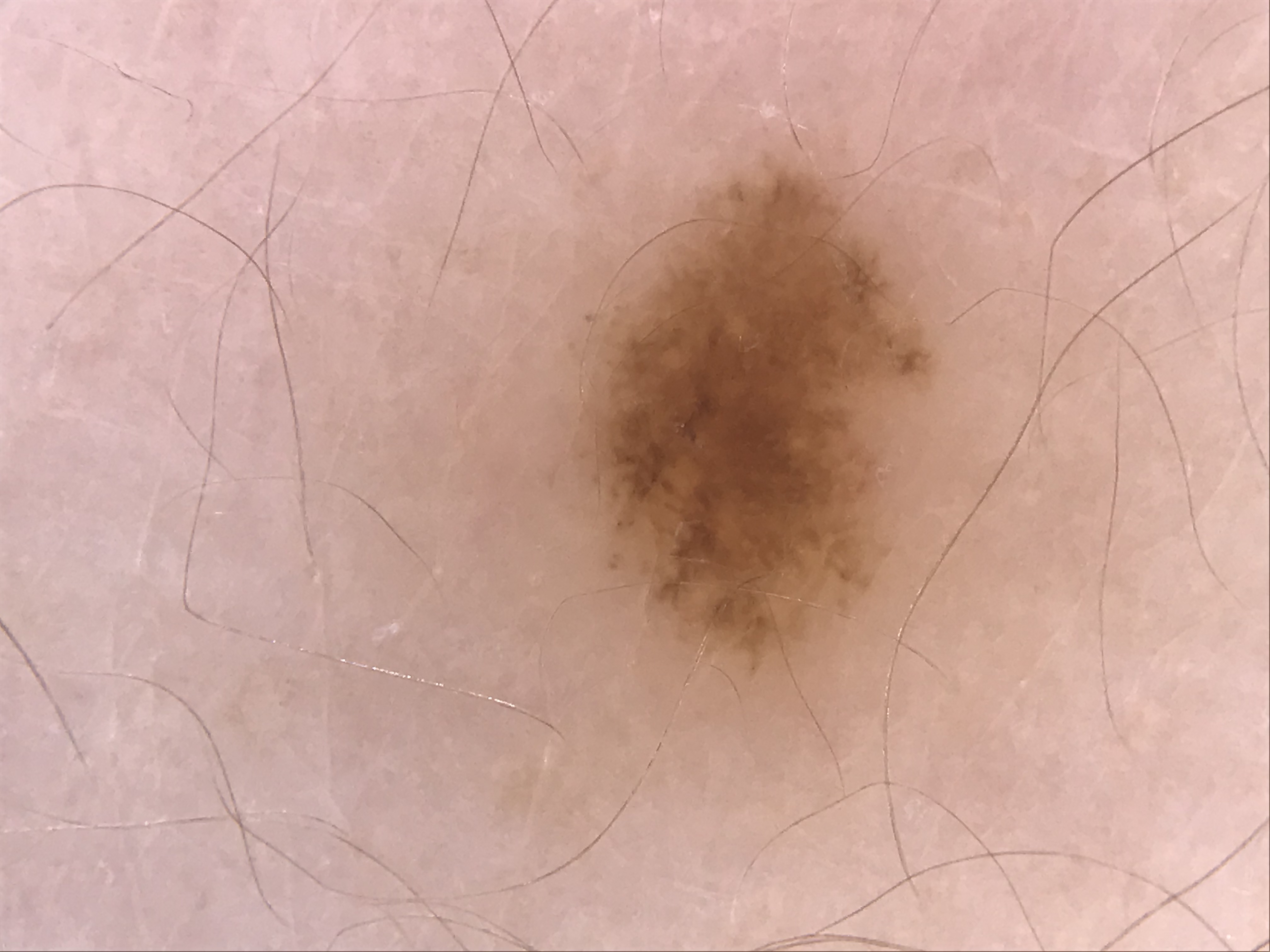Impression: Labeled as a dysplastic junctional nevus.